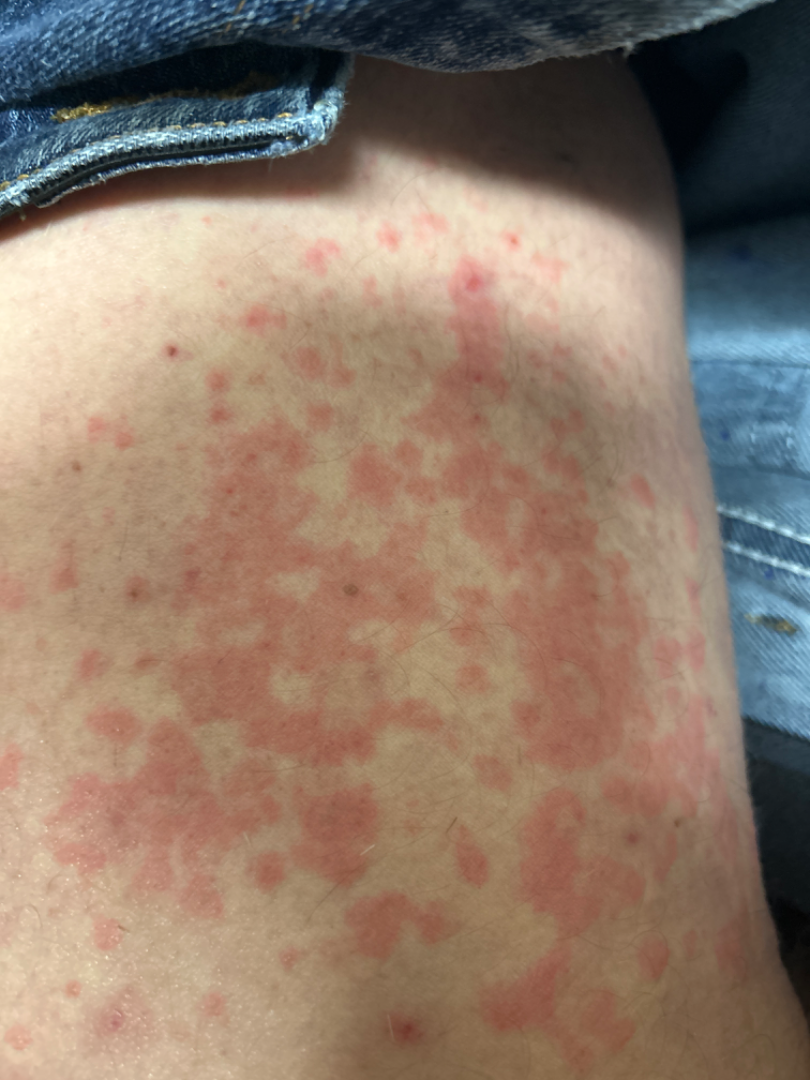assessment = indeterminate
framing = close-up
site = leg and back of the torso
described texture = flat